A male subject in their late 70s; a clinical photograph of a skin lesion — 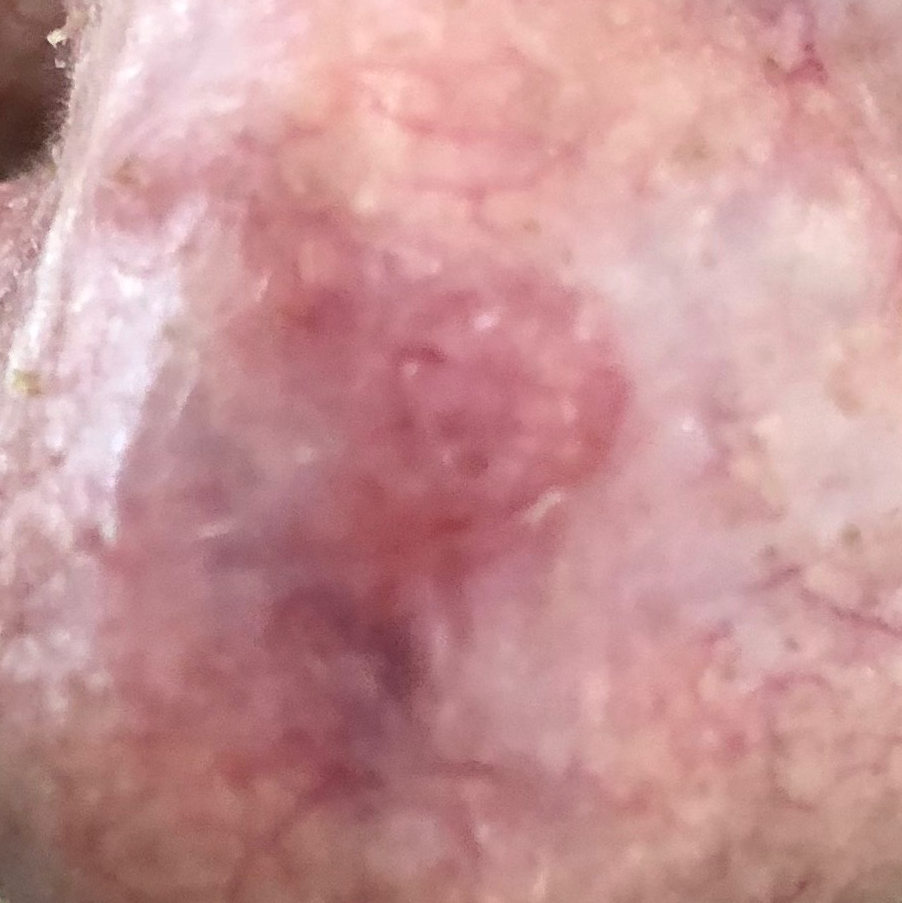{
  "lesion_location": "the nose",
  "symptoms": {
    "present": [
      "itching",
      "elevation"
    ]
  },
  "diagnosis": {
    "name": "basal cell carcinoma",
    "code": "BCC",
    "malignancy": "malignant",
    "confirmation": "histopathology"
  }
}